The patient was assessed as Fitzpatrick phototype II; a male patient about 75 years old; the chart notes a previous melanoma; a dermoscopy image of a single skin lesion — 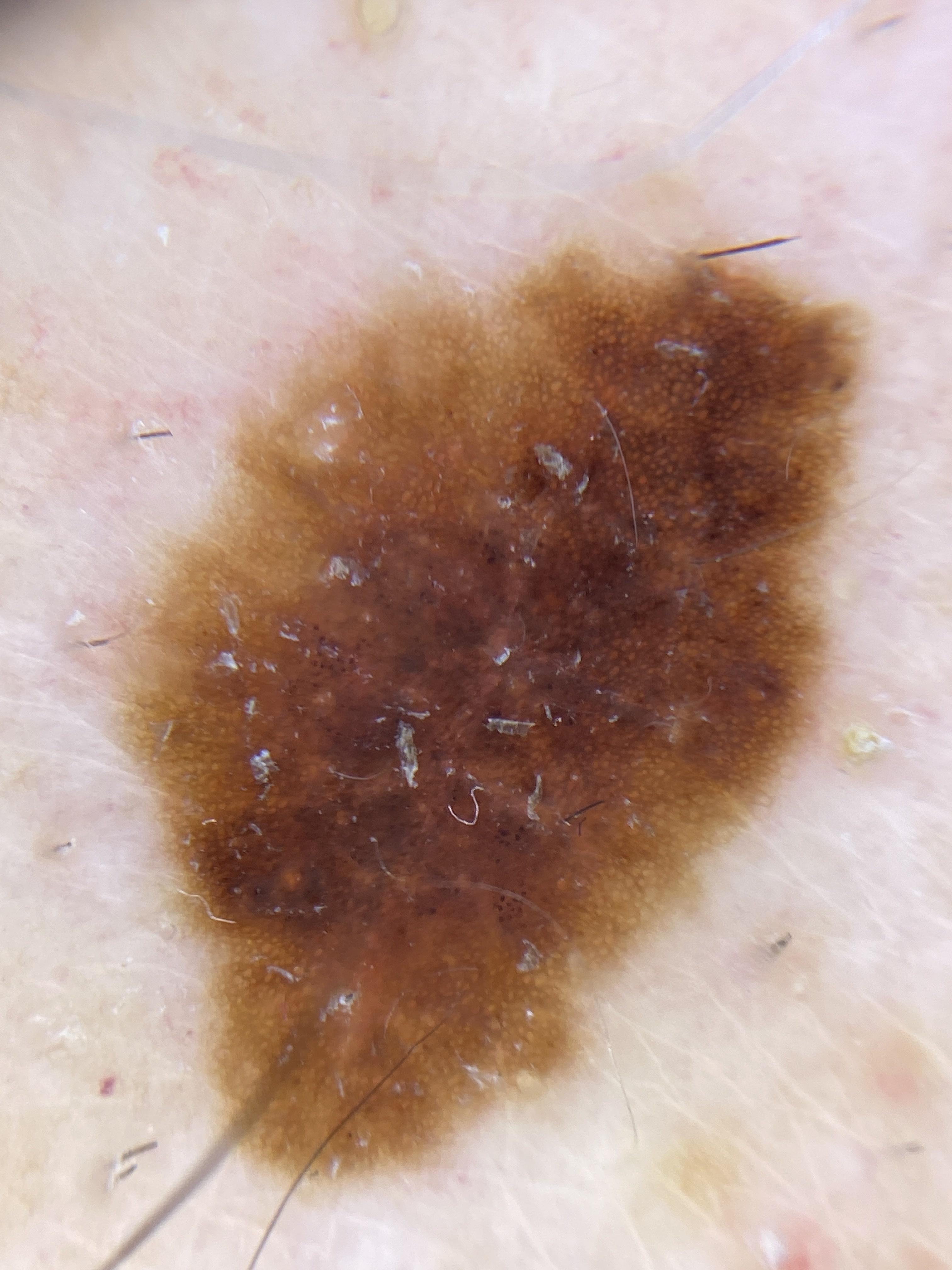Q: Where on the body is the lesion?
A: the trunk
Q: What is this lesion?
A: Nevus (biopsy-proven)